Dermoscopy of a skin lesion · a male patient, aged 73-77 — 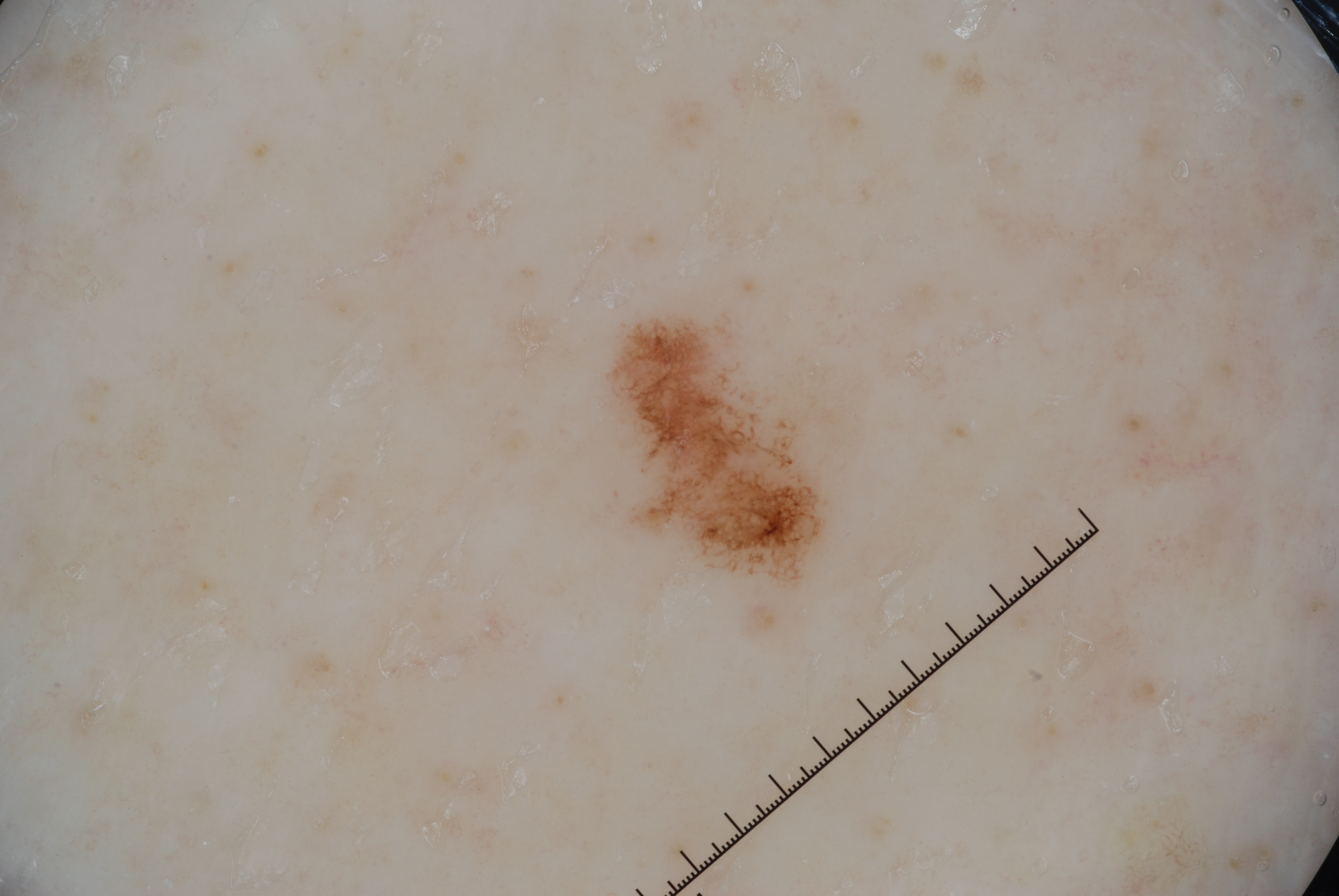Dermoscopic assessment notes pigment network; no milia-like cysts, negative network, or streaks.
In (x1, y1, x2, y2) order, the lesion's extent is [617, 322, 826, 574].
Expert review diagnosed this as a melanocytic nevus, a benign lesion.